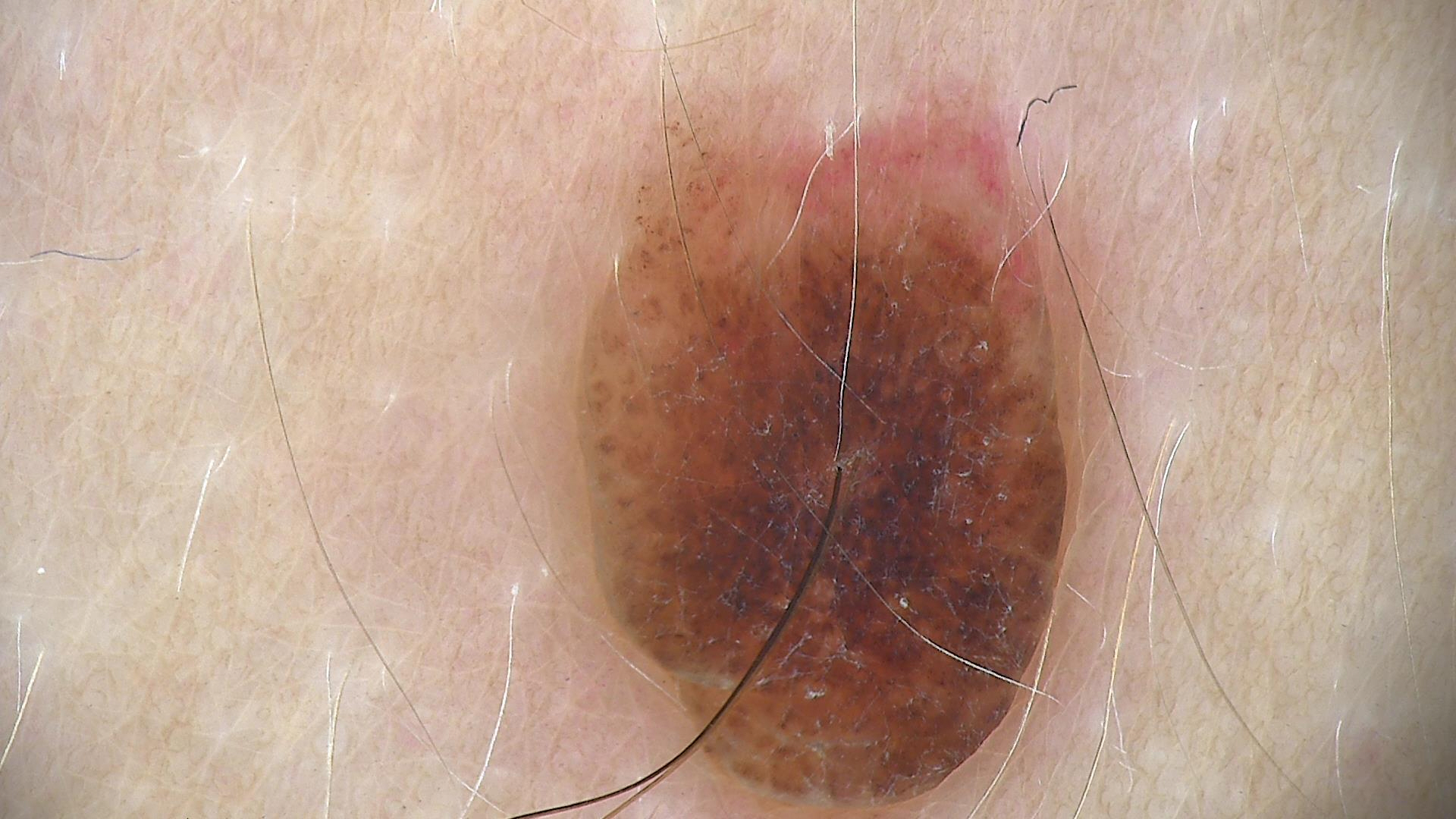This is a banal lesion. The diagnosis was a dermal nevus.